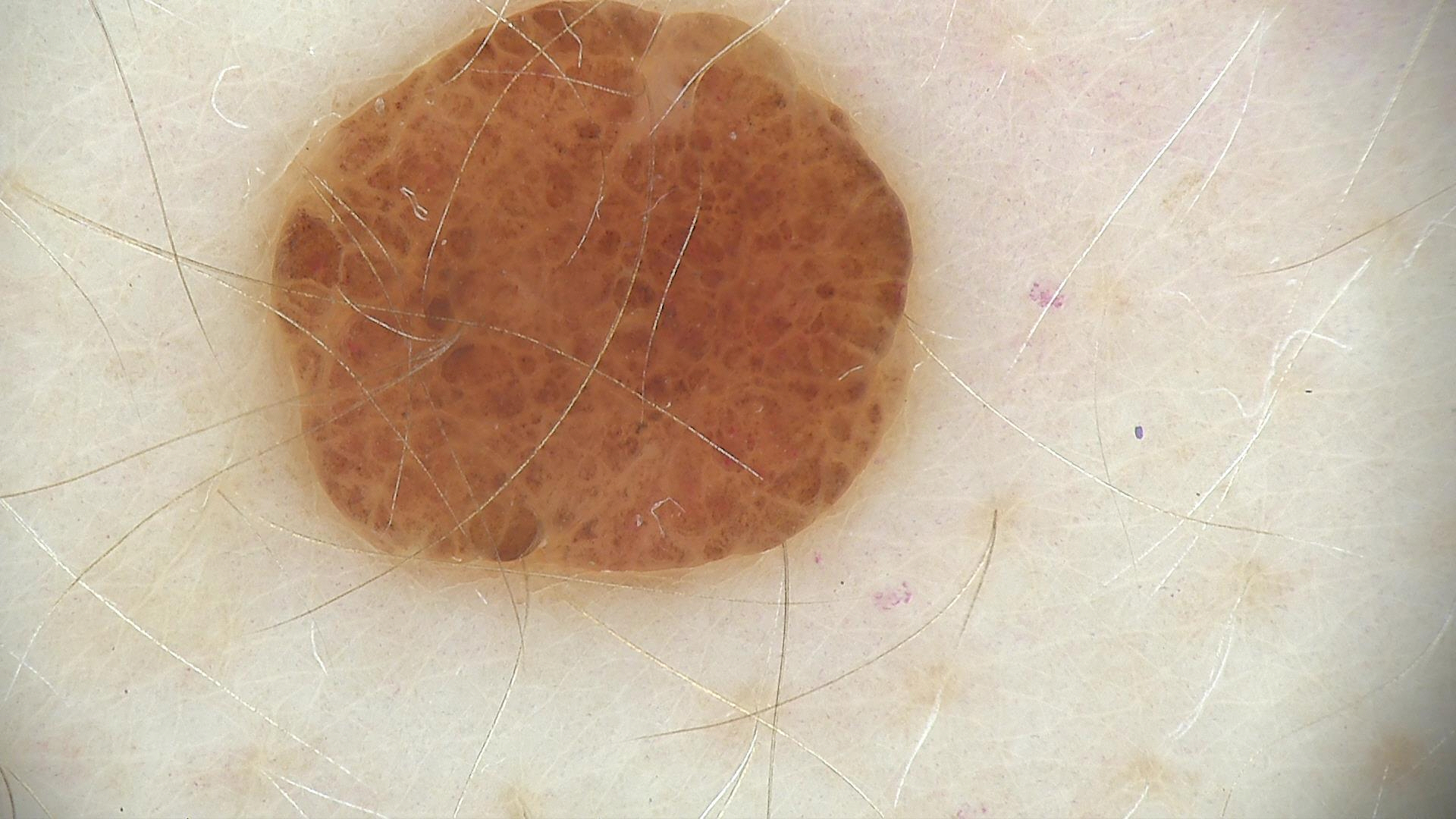modality: dermatoscopy, assessment: compound nevus (expert consensus).